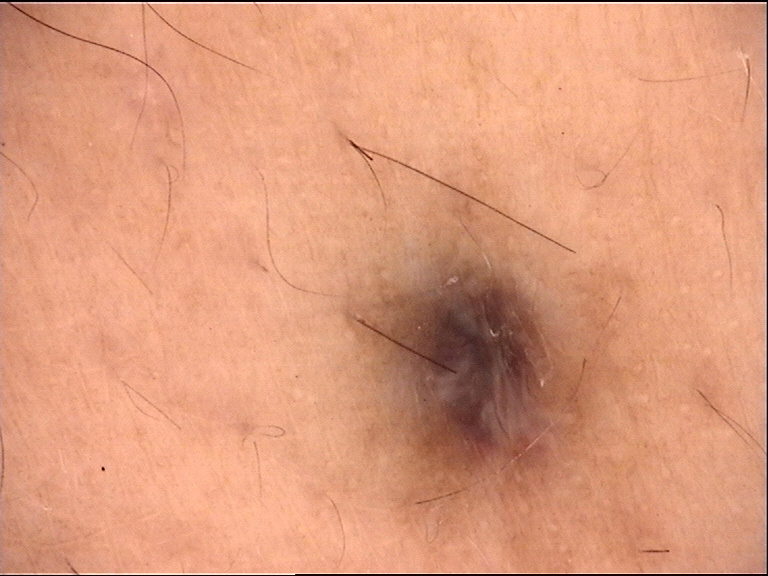modality = dermatoscopy | assessment = blue nevus (expert consensus).